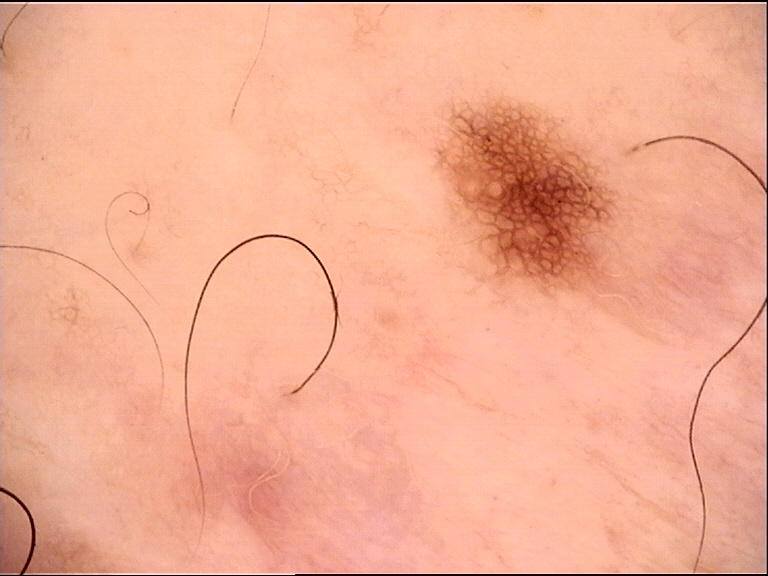Q: What is the imaging modality?
A: dermatoscopy
Q: What was the diagnostic impression?
A: dysplastic junctional nevus (expert consensus)